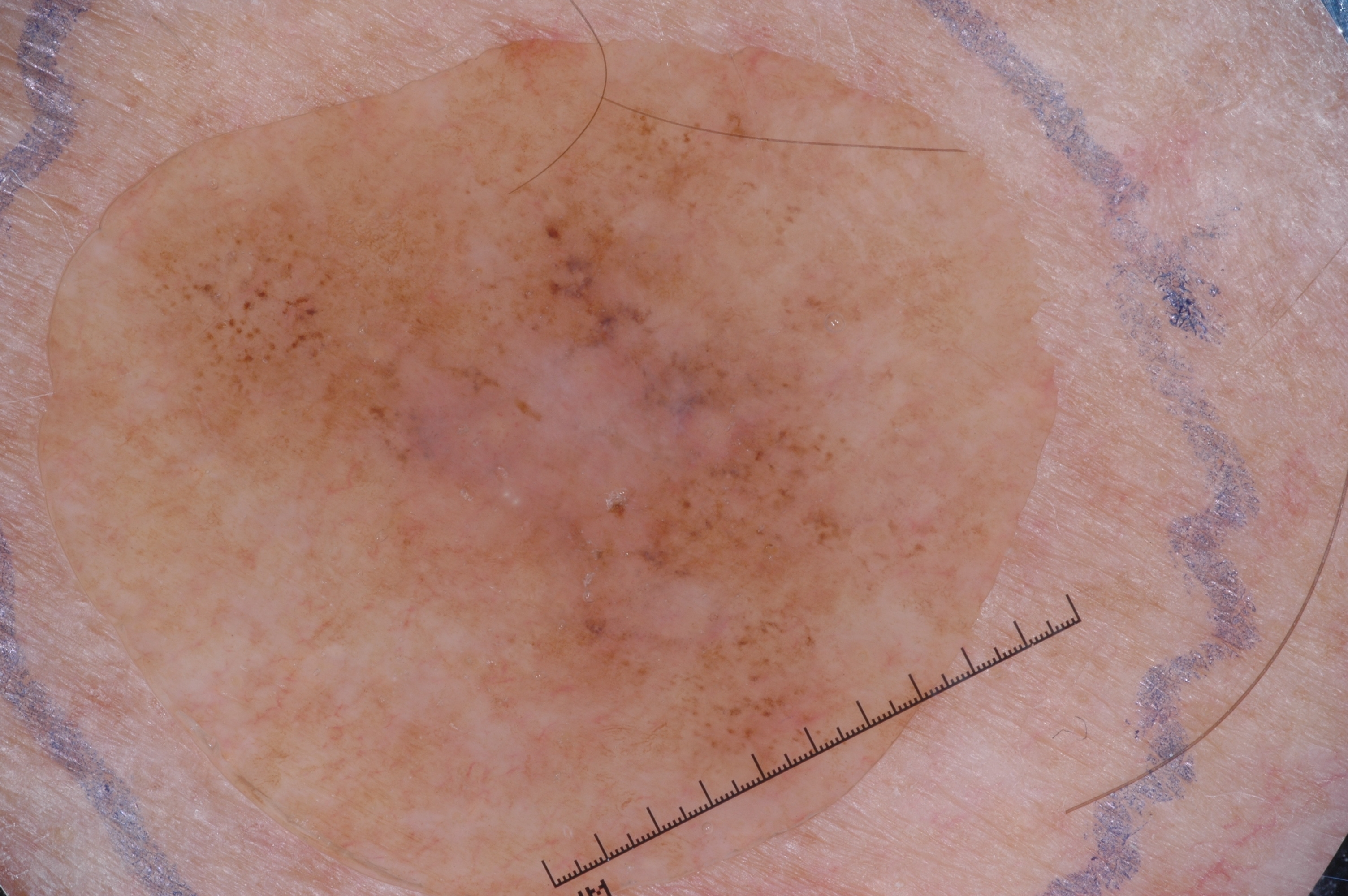A skin lesion imaged with a dermatoscope. The dermoscopic pattern shows milia-like cysts; no pigment network, streaks, or negative network. The lesion takes up a large portion of the image. Lesion location: x1=99, y1=80, x2=994, y2=861. Histopathological examination showed a melanoma, a malignant lesion.